The arm and leg are involved · a close-up photograph — 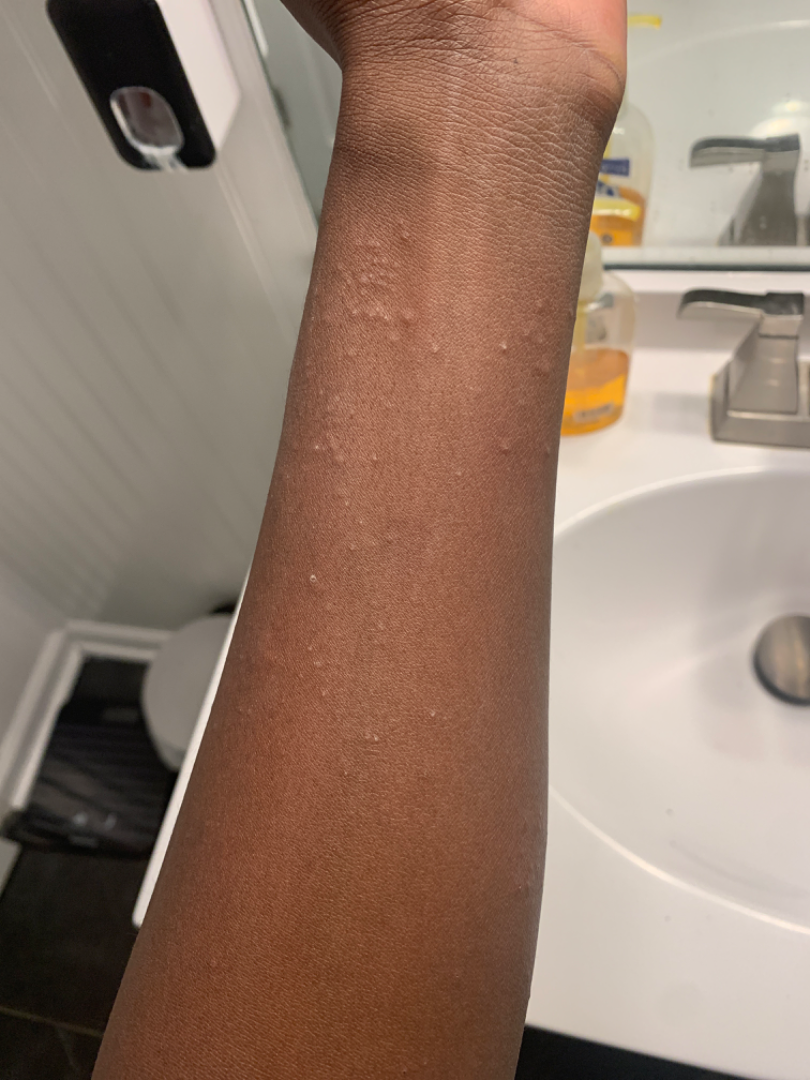described texture: flat
symptom duration: less than one week
self-categorized as: a rash
impression: Acute and chronic dermatitis (most likely)